Dermoscopy of a skin lesion.
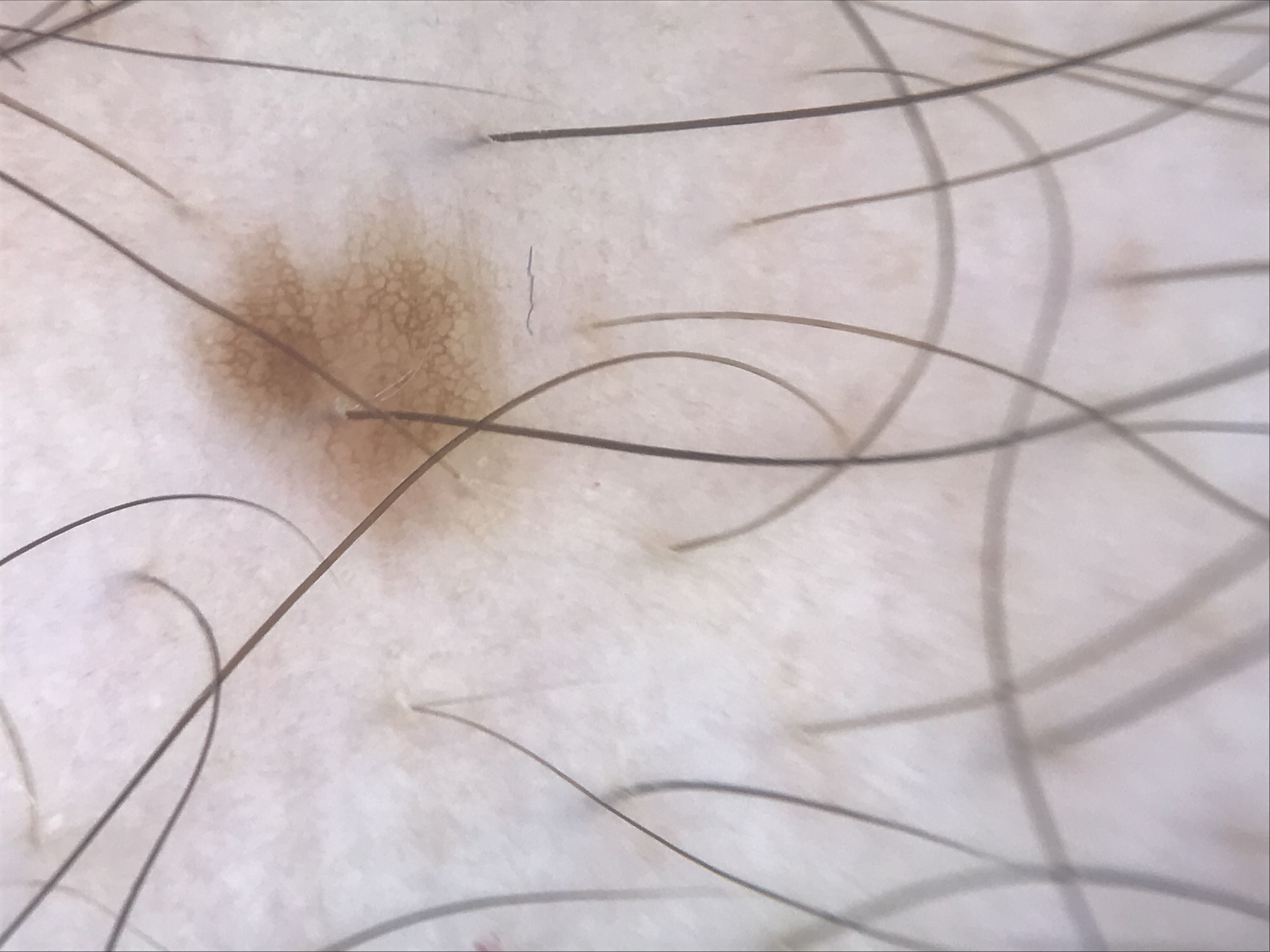Case:
The morphology is that of a banal lesion.
Conclusion:
Labeled as a junctional nevus.